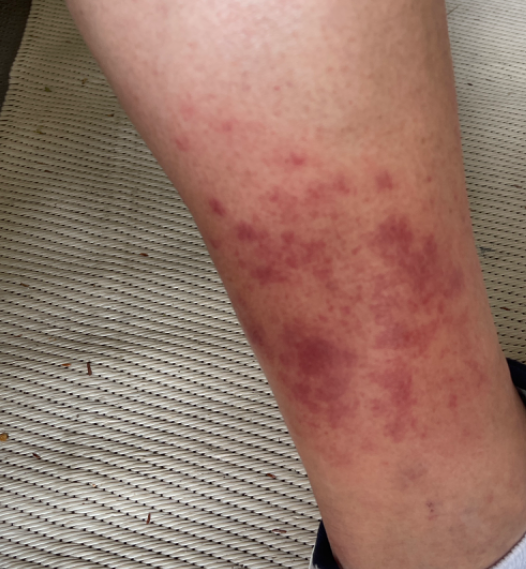Symptoms reported: pain, burning and itching.
The subject is male.
The photograph is a close-up of the affected area.
The leg is involved.
FST III; lay reviewers estimated Monk Skin Tone 3 (US pool) or 2 (India pool).
The patient considered this a rash.
The differential includes Purpura, Stasis Dermatitis and Leukocytoclastic Vasculitis, with no clear leading consideration.